The photograph is a close-up of the affected area · the leg is involved · no associated systemic symptoms reported · self-categorized by the patient as a rash · the contributor is a male aged 50–59 · the lesion is described as raised or bumpy · the contributor notes itching and burning — 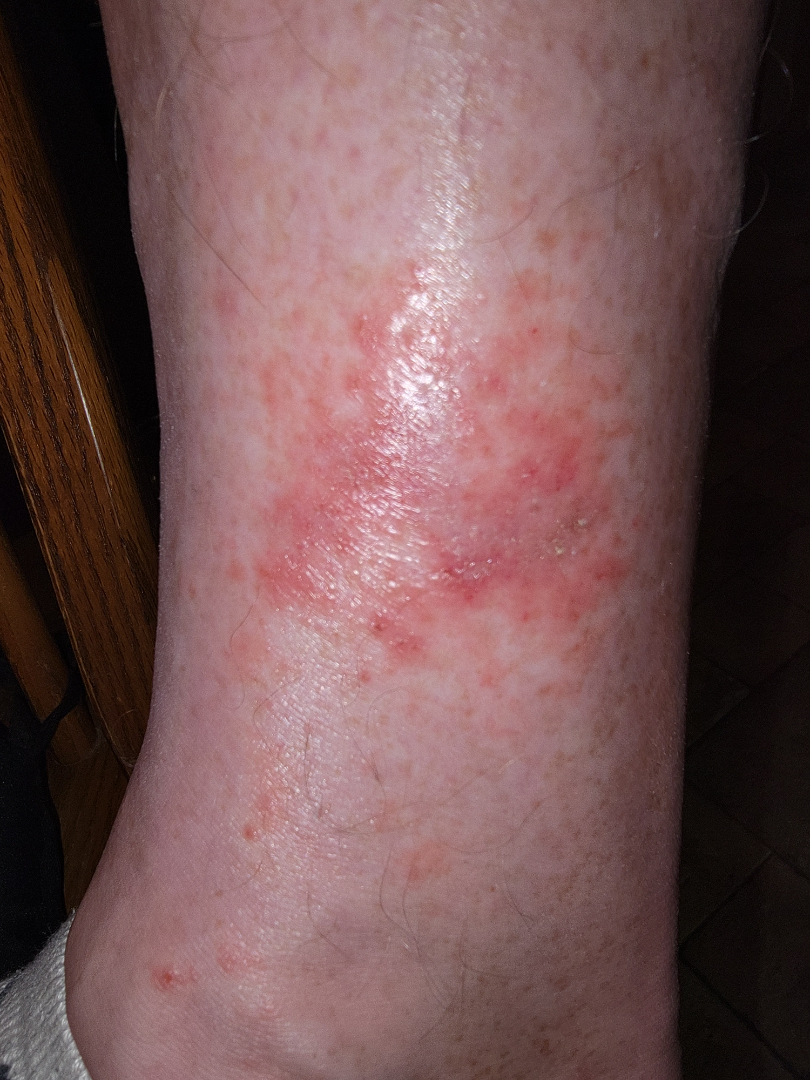• clinical impression — Stasis Dermatitis (38%); Irritant Contact Dermatitis (30%); Eczema (22%); Allergic Contact Dermatitis (10%)